Located on the front of the torso, leg, back of the hand, arm and top or side of the foot; the patient is a female aged 18–29; a close-up photograph: 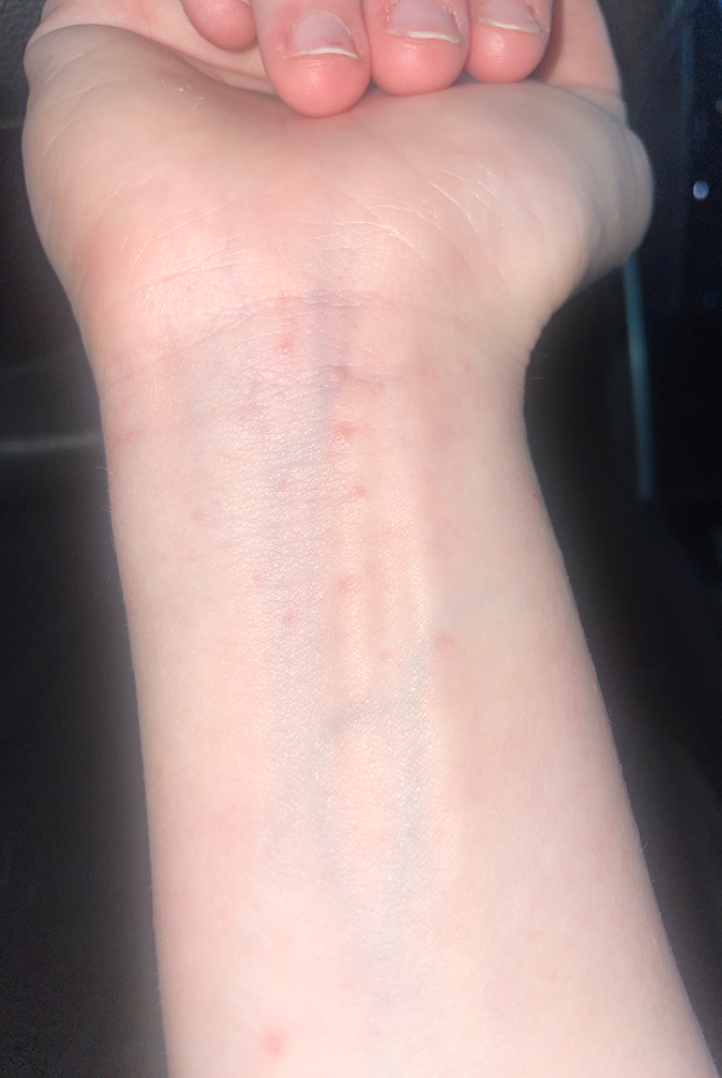Findings:
* differential diagnosis · three dermatologists each reviewed the case: favoring Eczema; possibly Irritant Contact Dermatitis; a remote consideration is Lichen planus/lichenoid eruption; less probable is Allergic Contact Dermatitis